The photograph was taken at an angle; the subject is male; the lesion involves the leg — 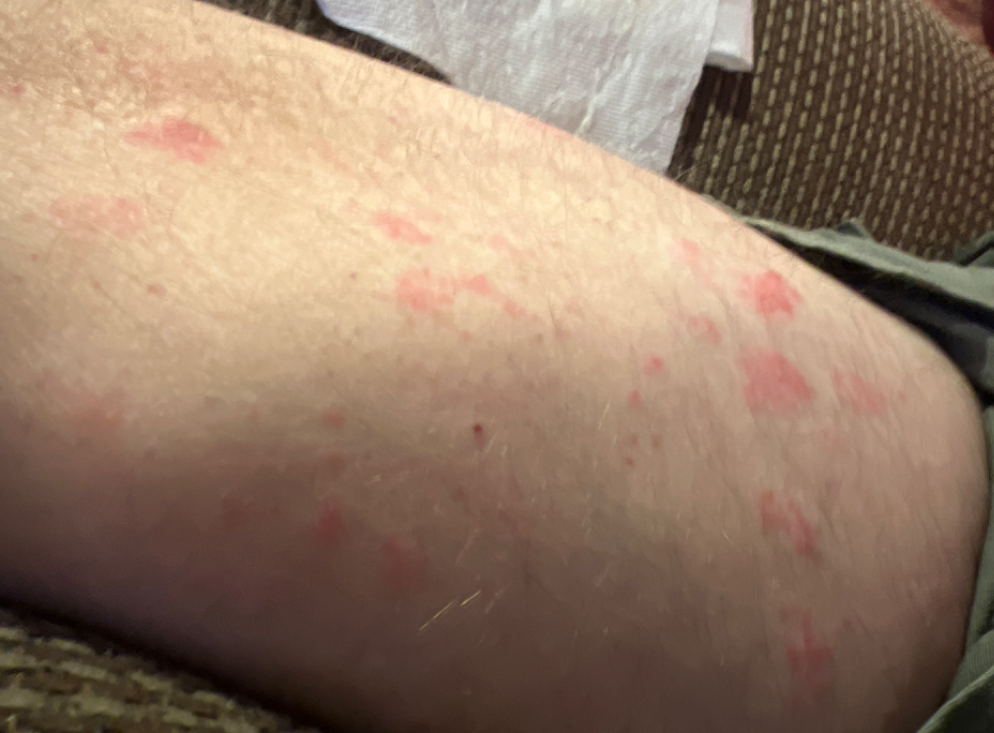The reviewing dermatologist was unable to assign a differential diagnosis from the image. Self-categorized by the patient as a rash. The contributor reports the lesion is rough or flaky and raised or bumpy. The lesion is associated with bothersome appearance.